Few moles overall by the patient's own estimate. On a questionnaire the patient reported a personal history of cancer. The patient says their skin reddens with sun exposure. A dermoscopy image of a skin lesion. A male subject 78 years of age. Collected as part of a research study, without a referral diagnosis: 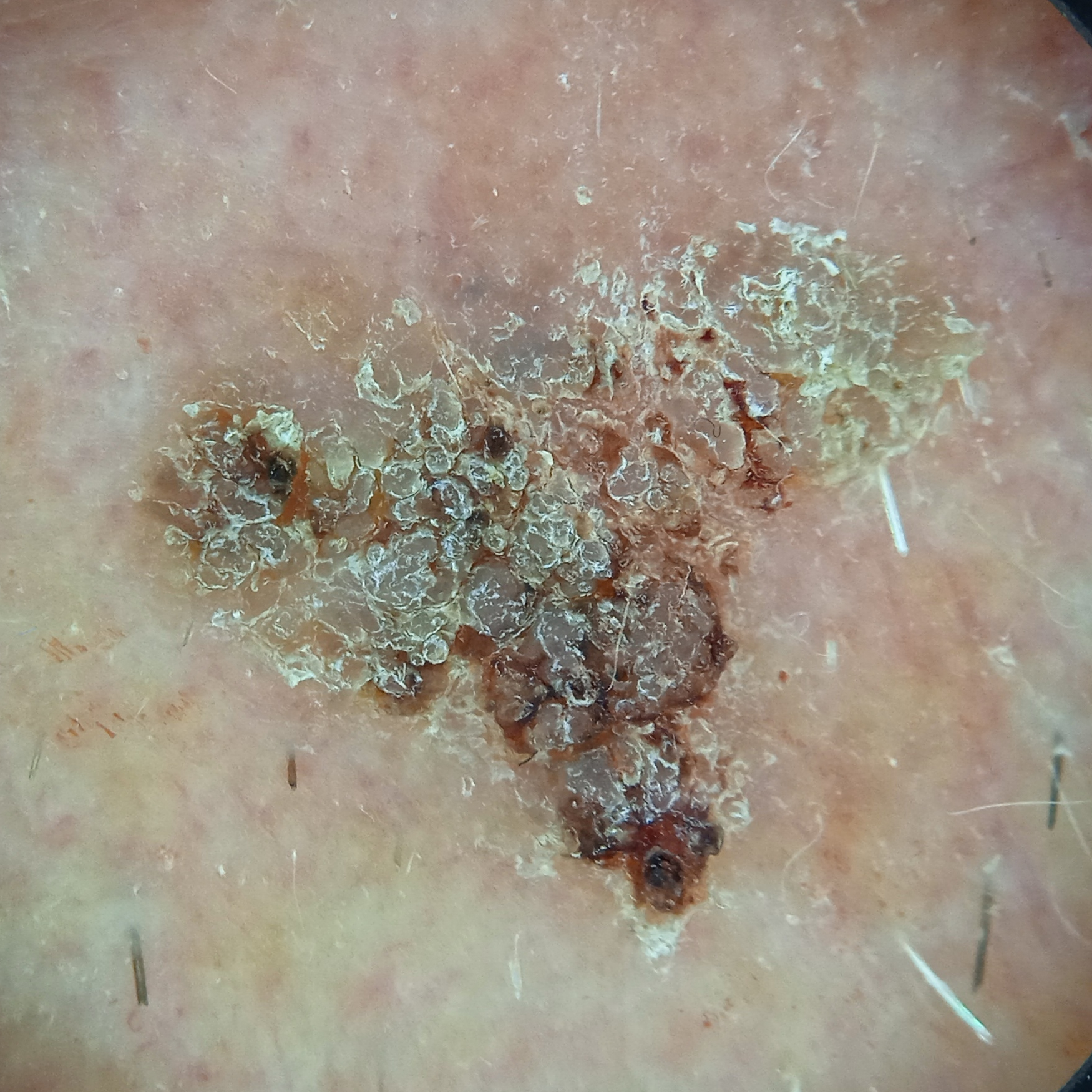Findings: The lesion involves the face. The lesion is about 10.5 mm across. Assessment: Dermatologist review favored a seborrheic keratosis.